A subject in their 70s; a clinical close-up photograph of a skin lesion: 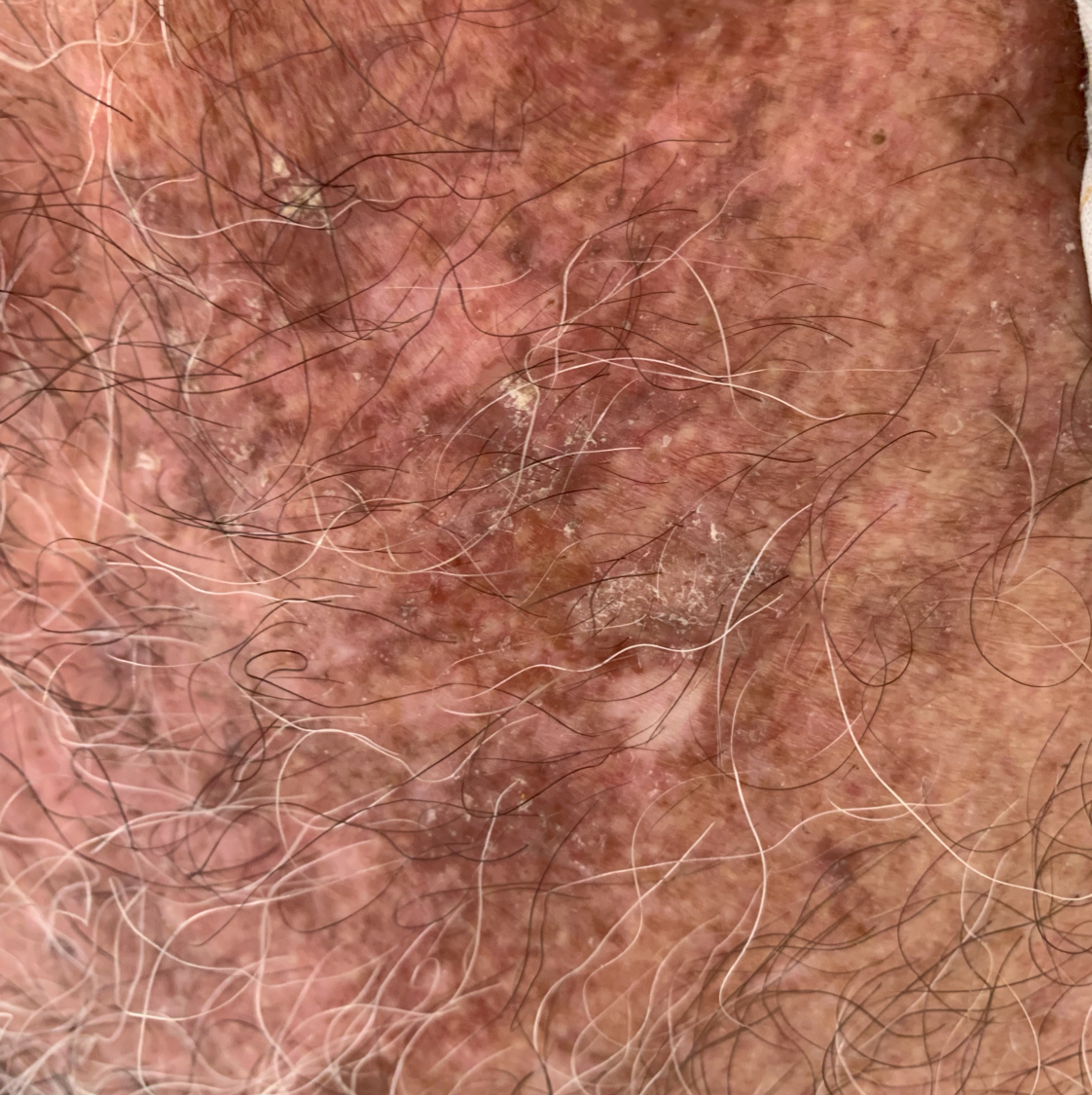  lesion_location: a forearm
  diagnosis:
    name: actinic keratosis
    code: ACK
    malignancy: indeterminate
    confirmation: clinical consensus